The patient indicates the condition has been present for less than one week; the affected area is the leg, back of the hand and arm; close-up view; the contributor is a male aged 18–29:
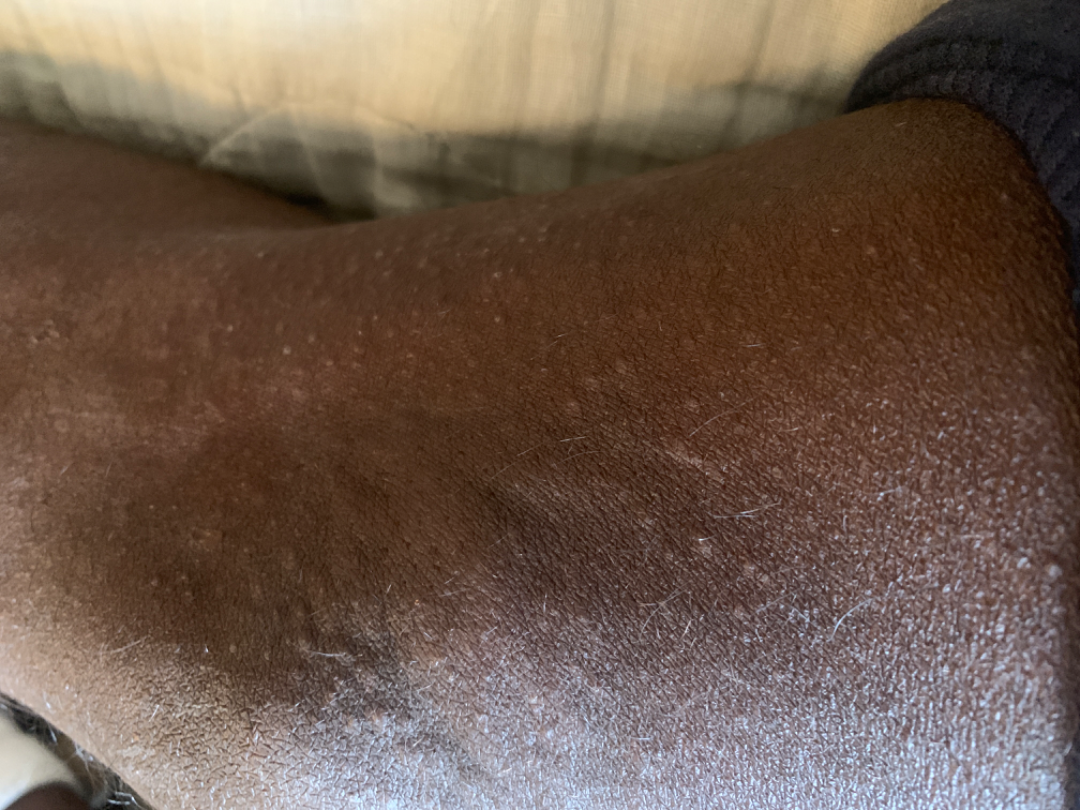| feature | finding |
|---|---|
| assessment | Eczema (1.00) |